Close-up view · the affected area is the leg · the subject is a female aged 70–79.
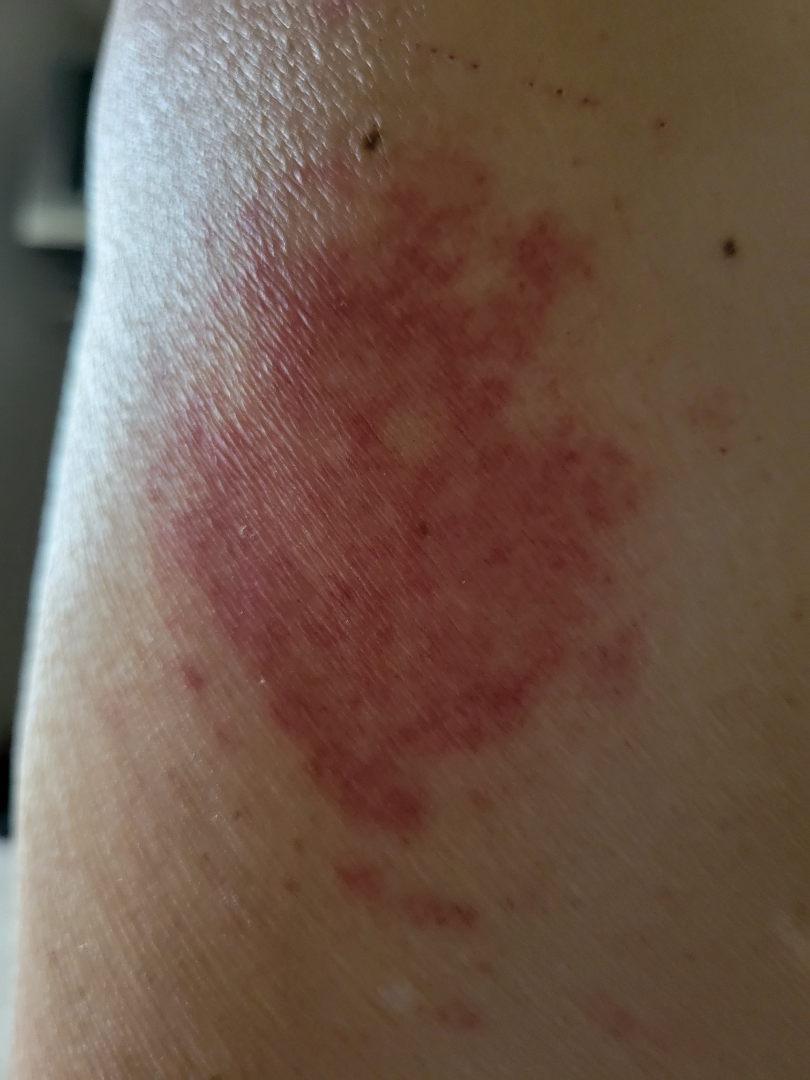On photographic review, the differential, in no particular order, includes Hemangioma and ecchymoses; a more distant consideration is Angiosarcoma of skin.